A dermoscopy image of a single skin lesion — 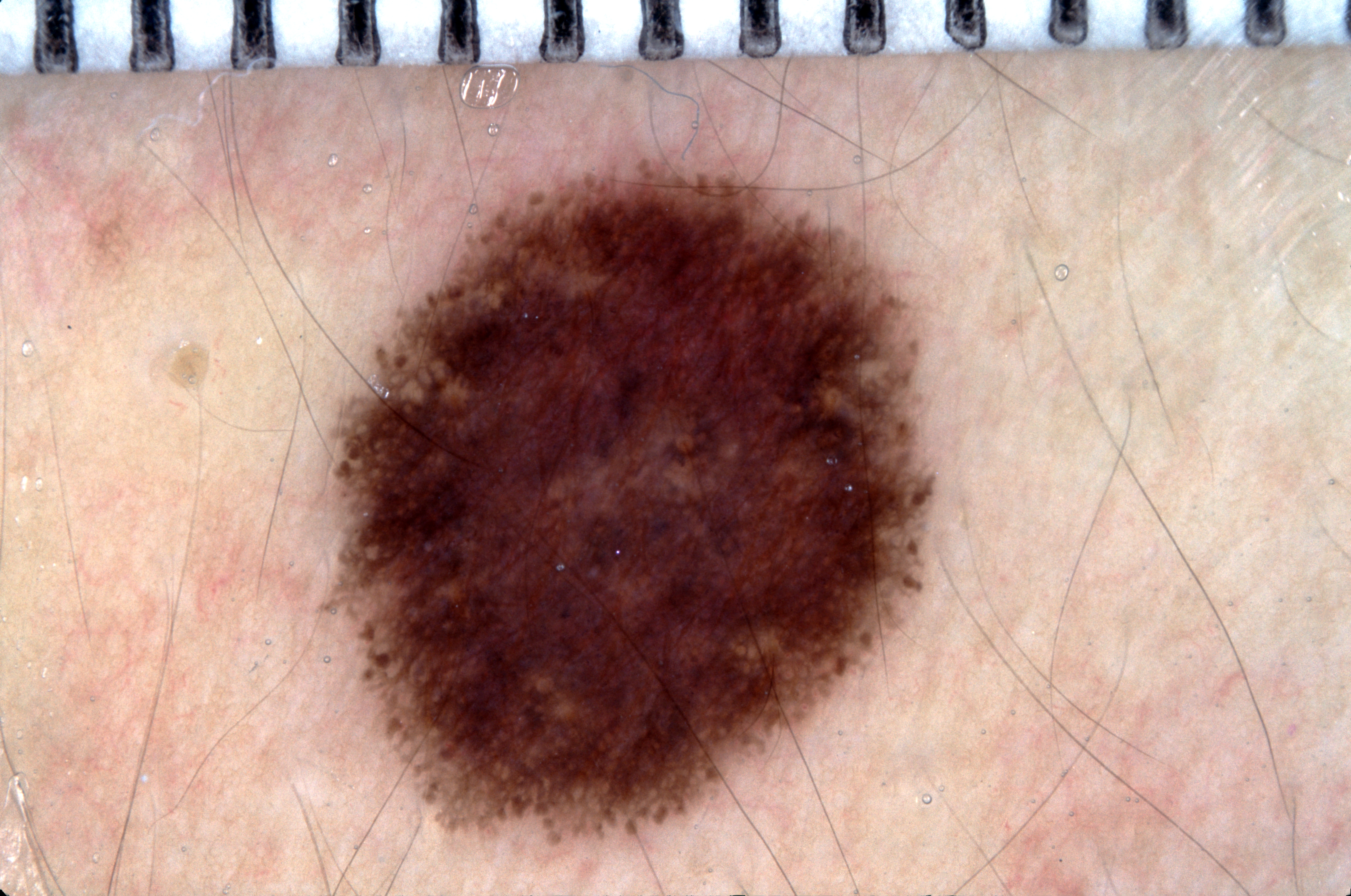<lesion>
<lesion_extent>moderate</lesion_extent>
<dermoscopic_features>
  <present>pigment network</present>
  <absent>milia-like cysts, streaks, negative network</absent>
</dermoscopic_features>
<lesion_location>
  <bbox_xyxy>321, 154, 935, 844</bbox_xyxy>
</lesion_location>
<diagnosis>
  <name>melanocytic nevus</name>
  <malignancy>benign</malignancy>
  <lineage>melanocytic</lineage>
  <provenance>clinical</provenance>
</diagnosis>
</lesion>